This is a dermoscopic photograph of a skin lesion, a female subject roughly 15 years of age — 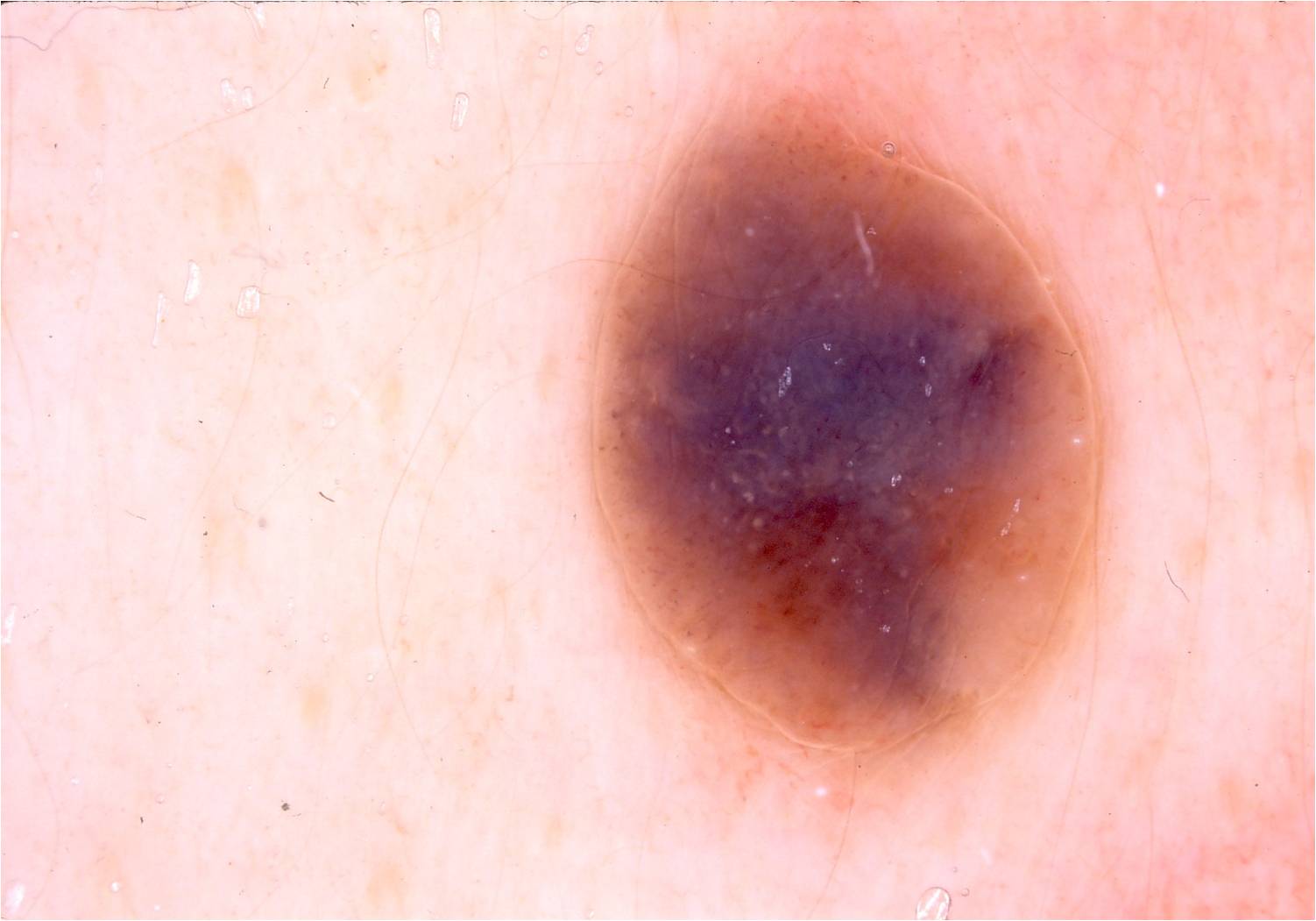The visible lesion spans [594,72,1100,752]. Dermoscopy demonstrates no milia-like cysts, pigment network, negative network, globules, or streaks. The diagnostic assessment was a melanocytic nevus.